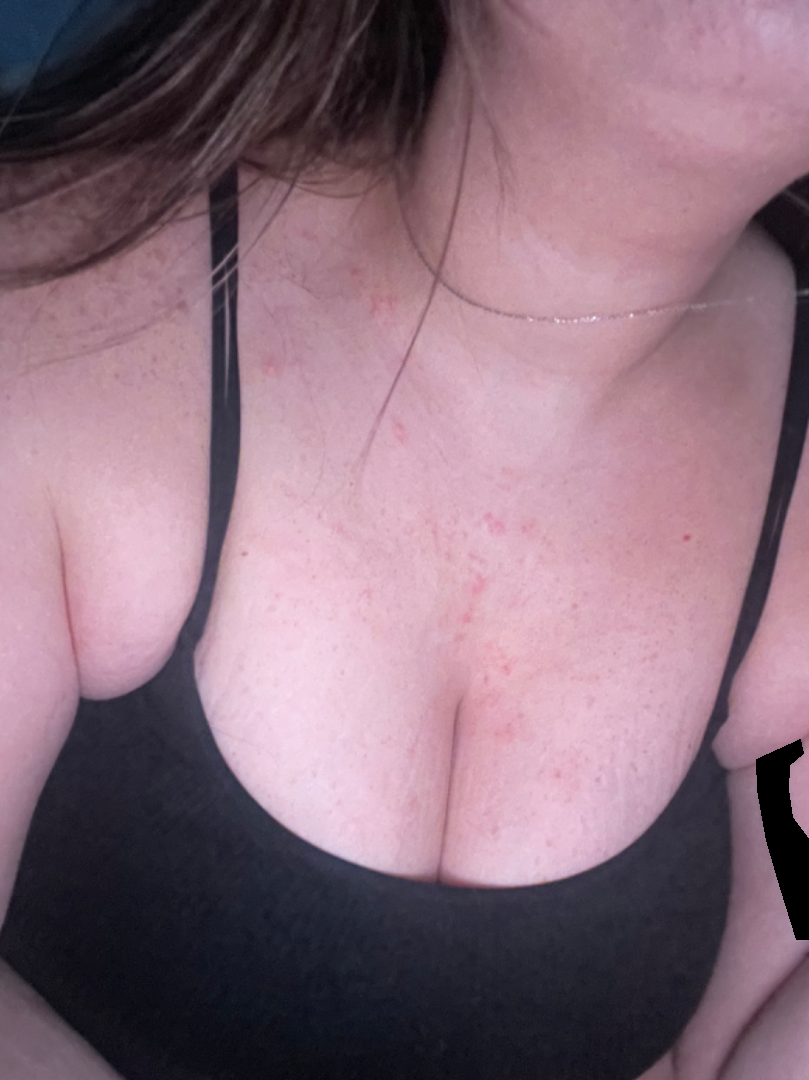Q: How does the lesion feel?
A: fluid-filled
Q: Patient's own categorization?
A: a rash
Q: Image view?
A: close-up
Q: Patient demographics?
A: female
Q: How long has this been present?
A: about one day
Q: Anatomic location?
A: front of the torso and head or neck
Q: Fitzpatrick or Monk tone?
A: Fitzpatrick skin type II; non-clinician graders estimated Monk Skin Tone 2
Q: What is the dermatologist's impression?
A: most likely Folliculitis; with consideration of Acne; also raised was Eczema